Close-up view. Female subject, age 40–49. The lesion involves the top or side of the foot and leg:
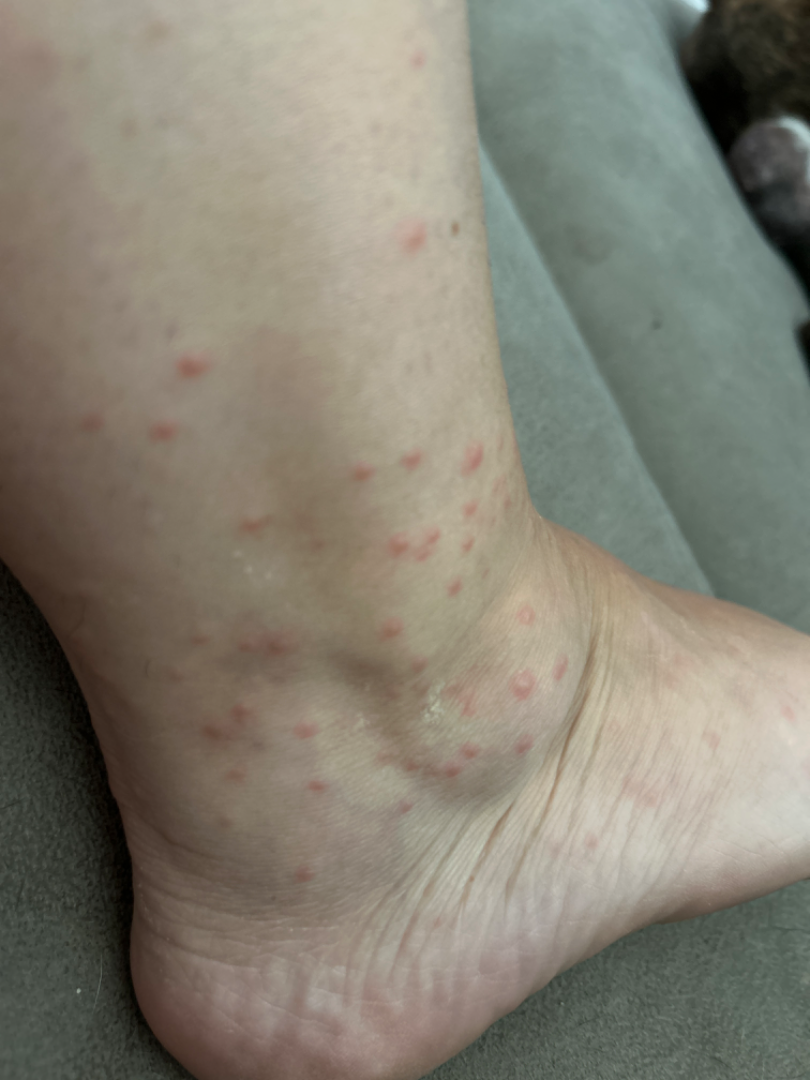Case summary:
– differential diagnosis — consistent with Insect Bite